The front of the torso is involved; female contributor, age 40–49; close-up view — 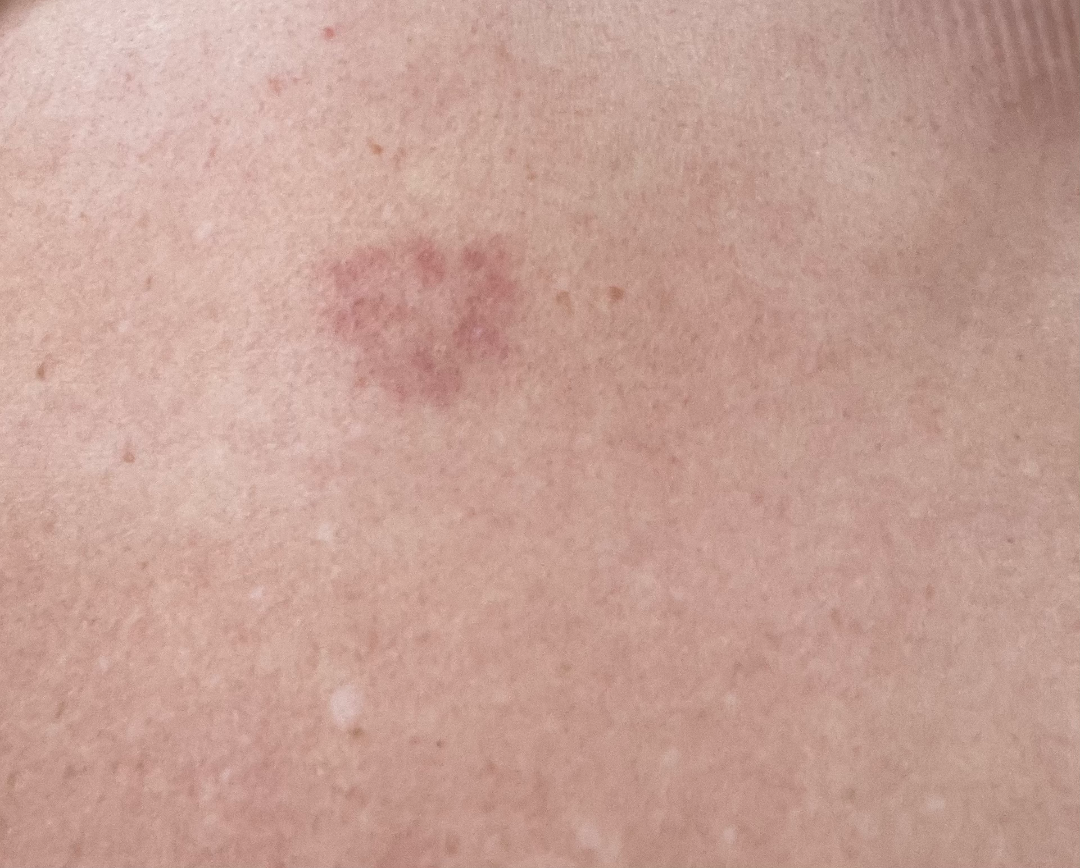Impression:
Favoring ecchymoses; an alternative is Hemangioma; the differential also includes Post-Inflammatory hyperpigmentation.